A dermoscopic image of a skin lesion.
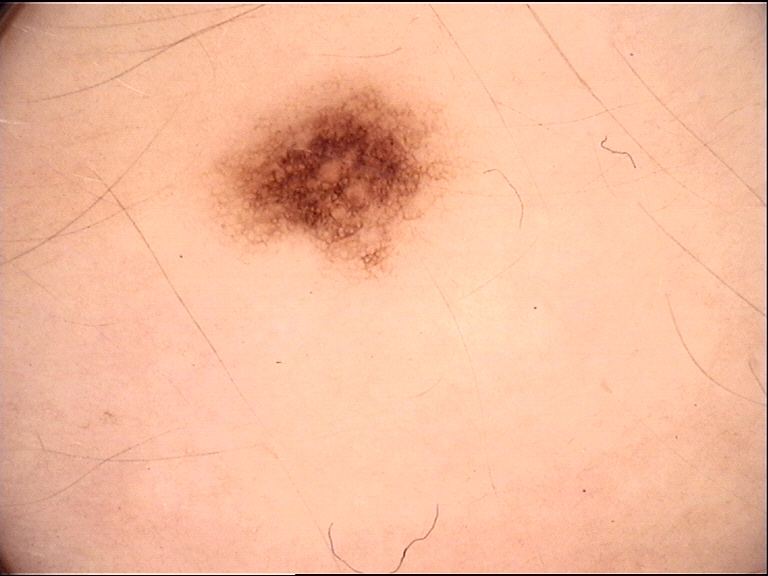Impression:
Labeled as a dysplastic junctional nevus.